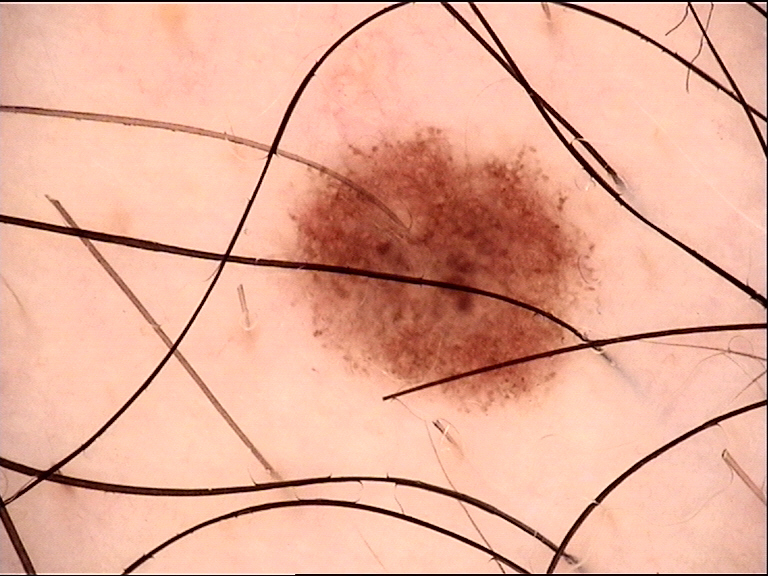diagnosis: dysplastic junctional nevus (expert consensus).